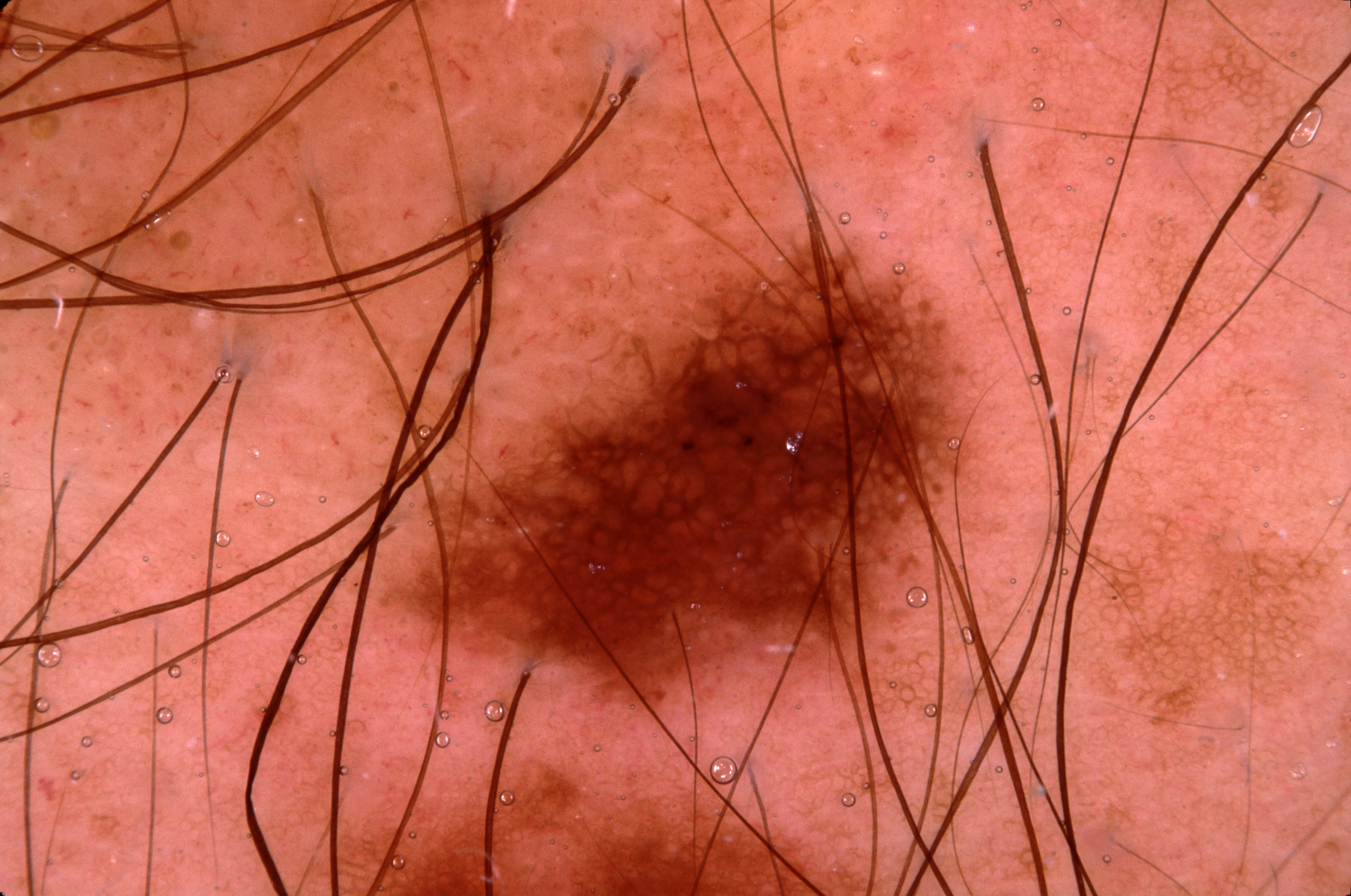Case summary:
* image: dermoscopy
* location: left=352, top=191, right=1003, bottom=727
* size: moderate
* dermoscopic features: milia-like cysts and pigment network
* diagnosis: a melanocytic nevus, a benign lesion